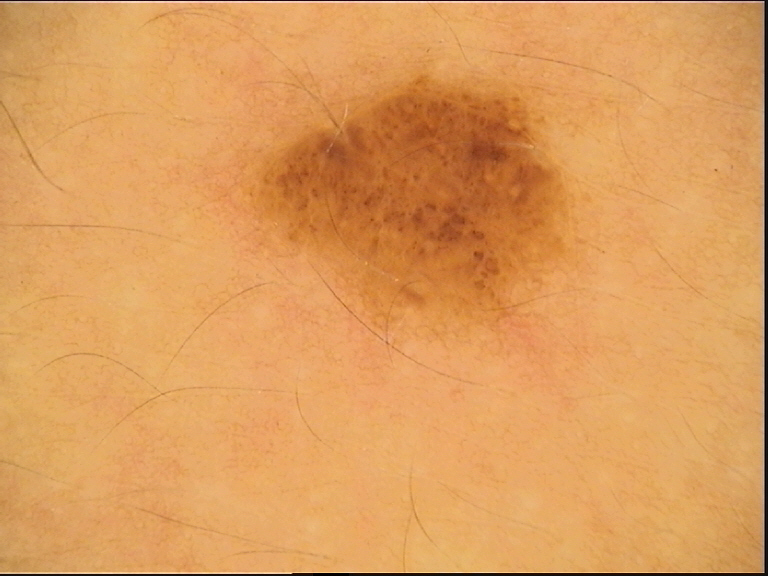Conclusion:
Consistent with a banal lesion — a compound nevus.